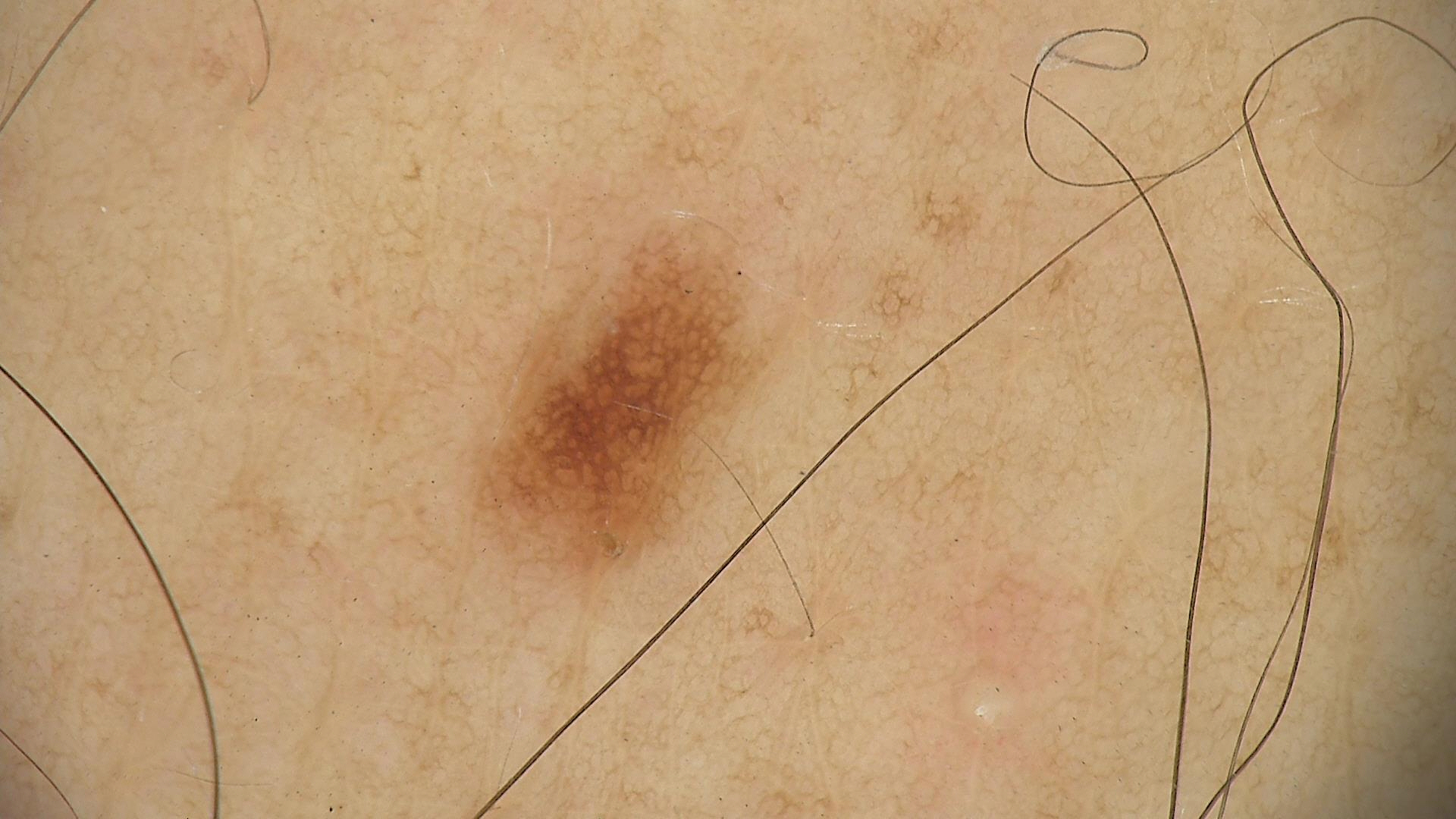Q: What is the imaging modality?
A: dermoscopy
Q: What is the diagnosis?
A: dysplastic junctional nevus (expert consensus)